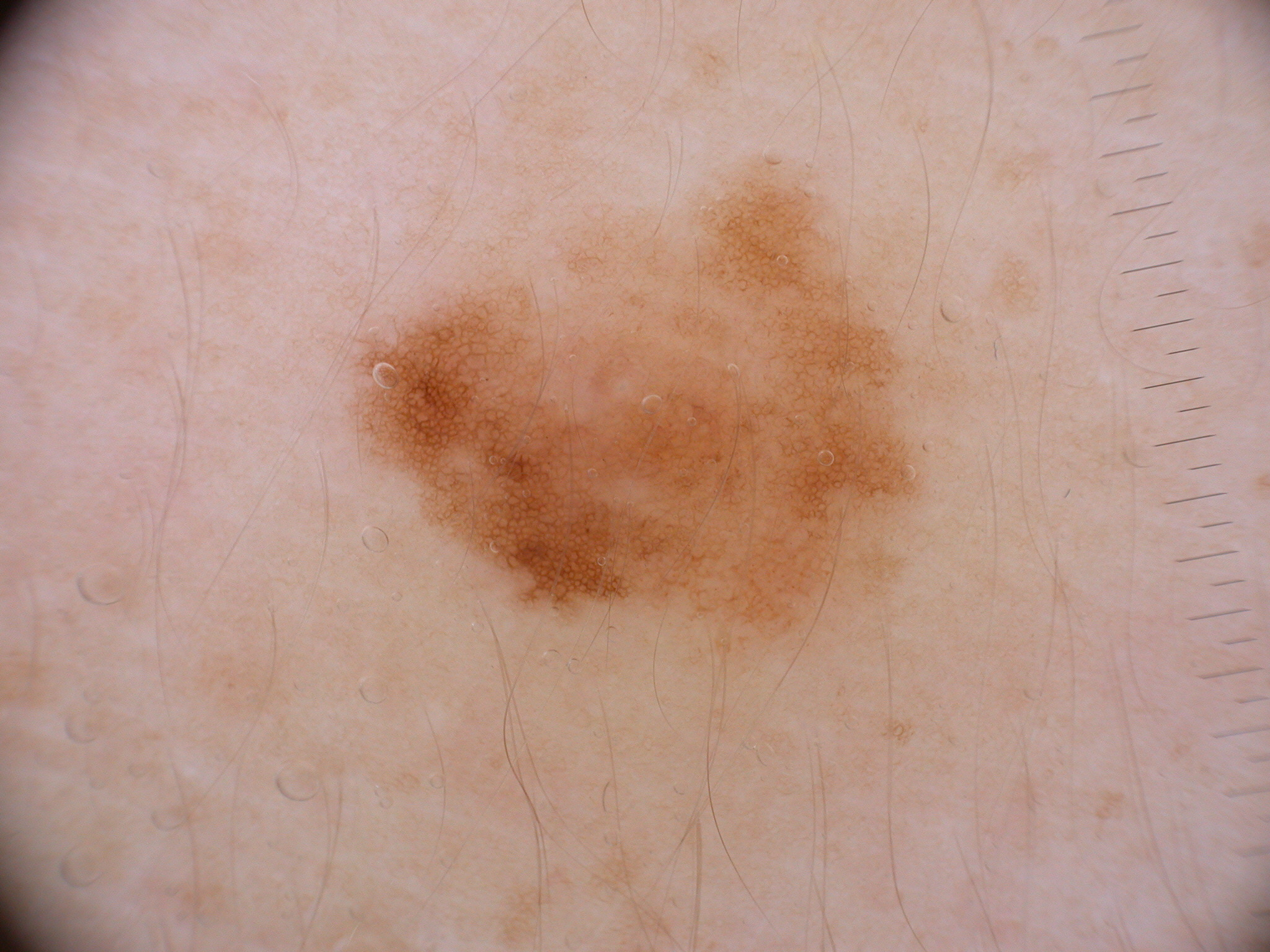| key | value |
|---|---|
| modality | dermoscopy of a skin lesion |
| location | 342/144/985/684 |
| dermoscopic features | pigment network |
| impression | a melanocytic nevus |